A skin lesion imaged with a dermatoscope: 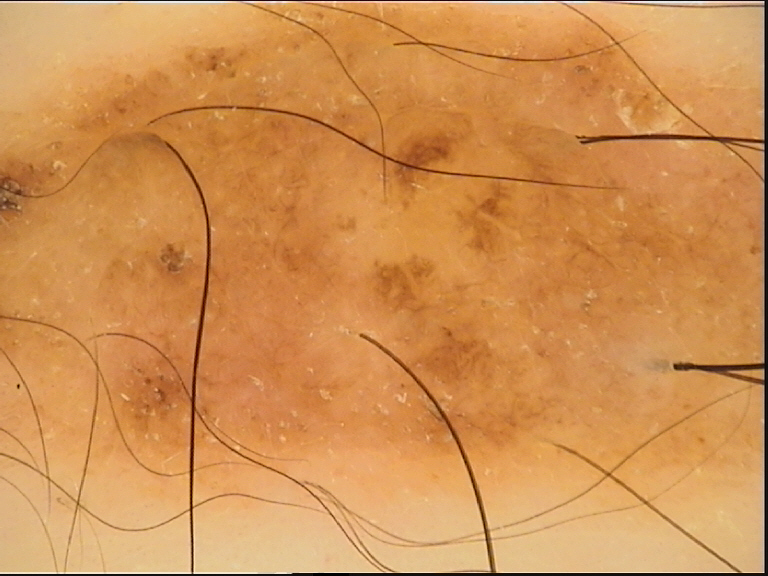assessment: dysplastic compound nevus (expert consensus).